A dermoscopic close-up of a skin lesion · a male subject, approximately 45 years of age.
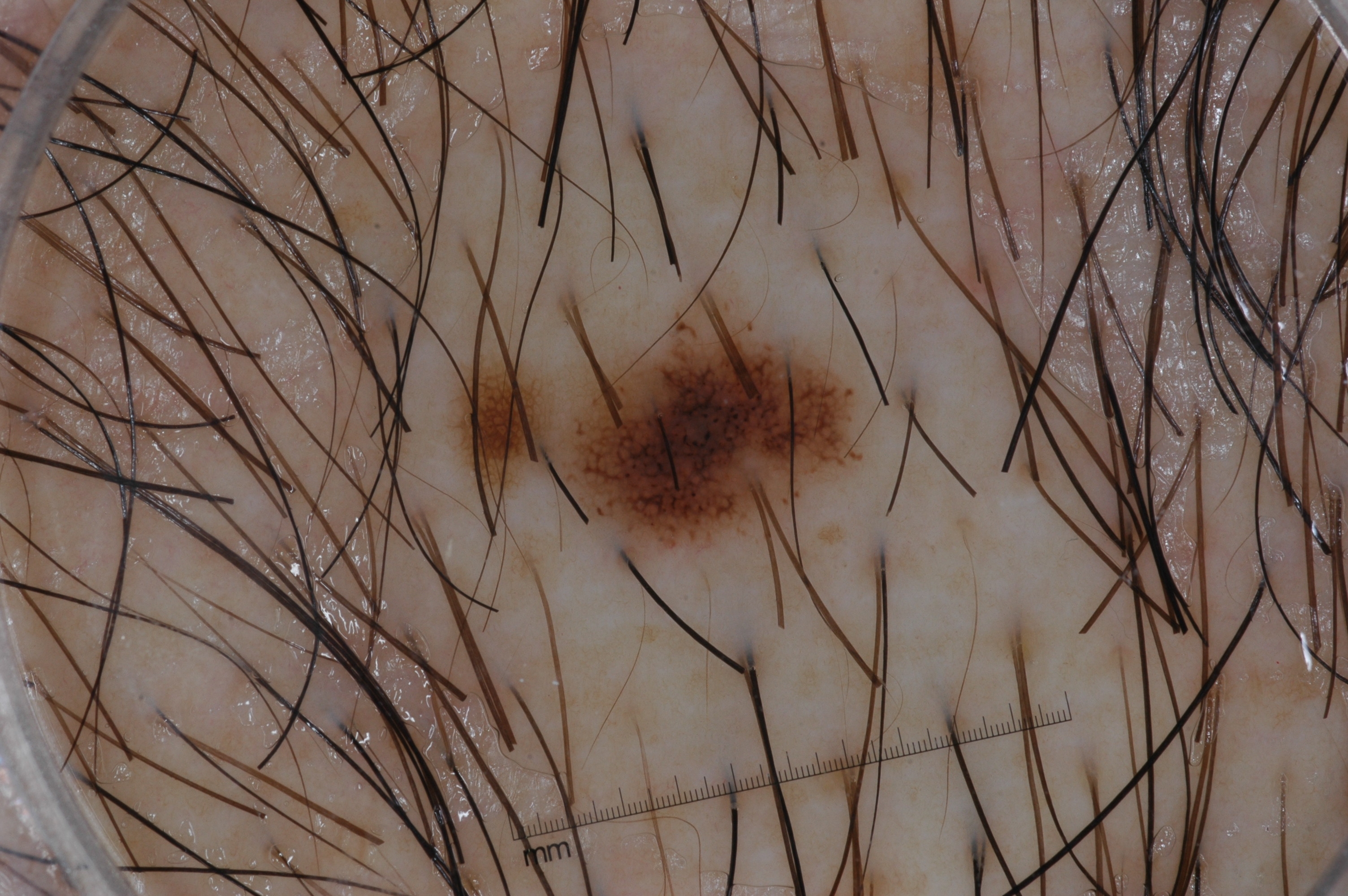Findings: The lesion is located at left=579, top=315, right=842, bottom=539. Dermoscopy demonstrates milia-like cysts and pigment network. The lesion occupies roughly 3% of the field. Conclusion: The lesion was assessed as a melanocytic nevus, a benign lesion.